The photo was captured at an angle; the subject is 18–29, male; the affected area is the back of the torso.
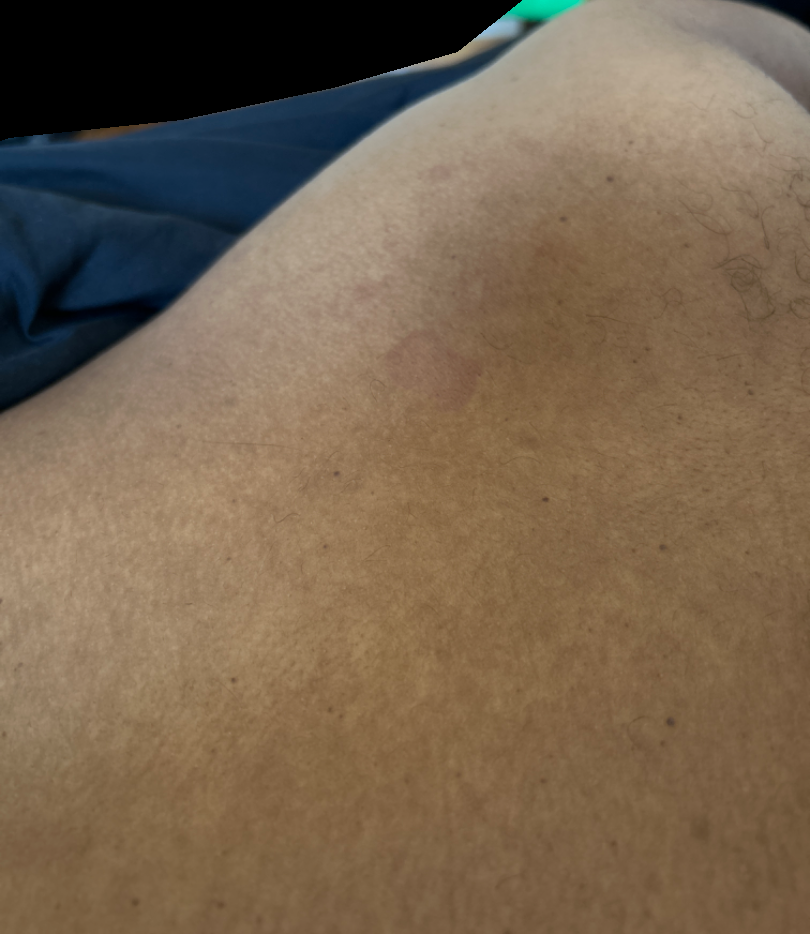dermatologist impression = Actinic Keratosis (considered); SCC/SCCIS (considered); Basal Cell Carcinoma (remote)